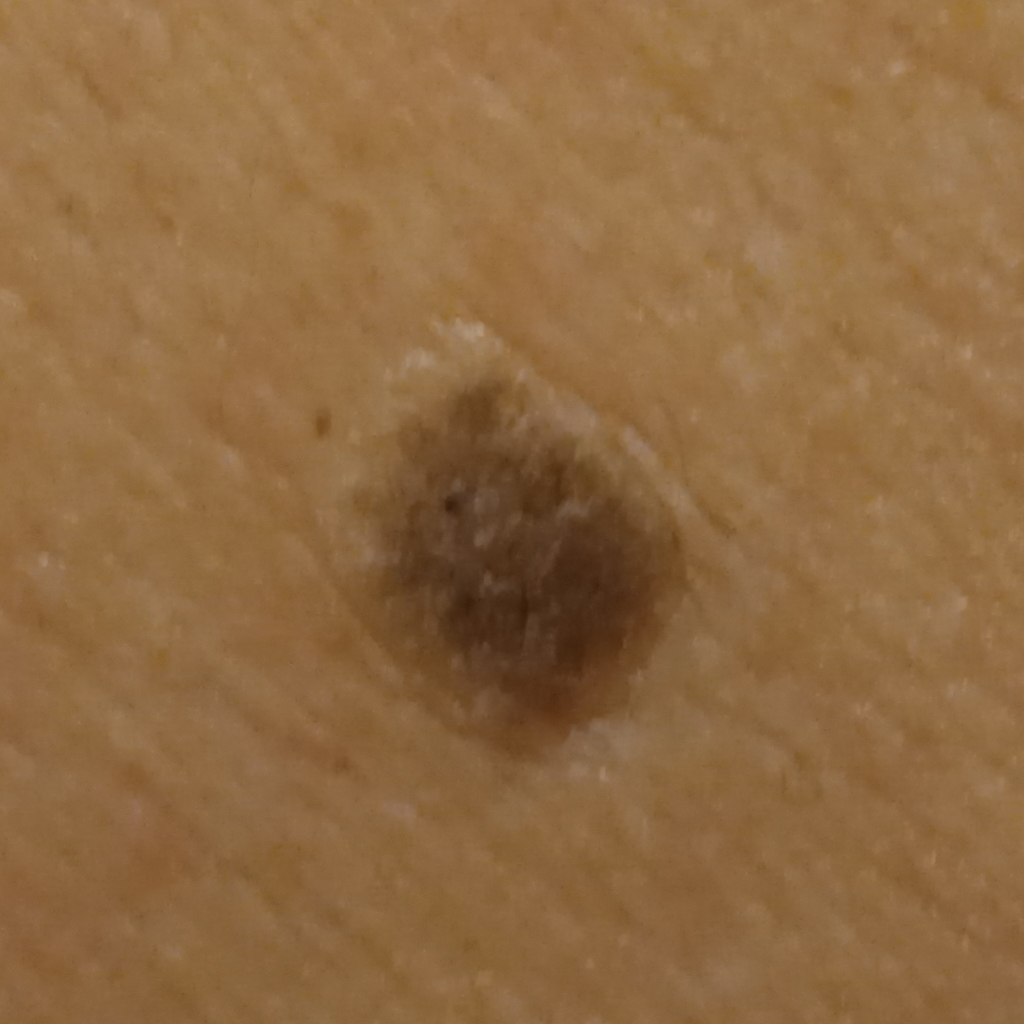Case summary: The patient says their skin tans without first burning. Few moles overall by the patient's own estimate. A male subject 67 years of age. The lesion involves the back. The lesion is about 8.9 mm across. Impression: The dermatologists' assessment was a seborrheic keratosis.